A clinical photograph showing a skin lesion; a female subject in their 50s:
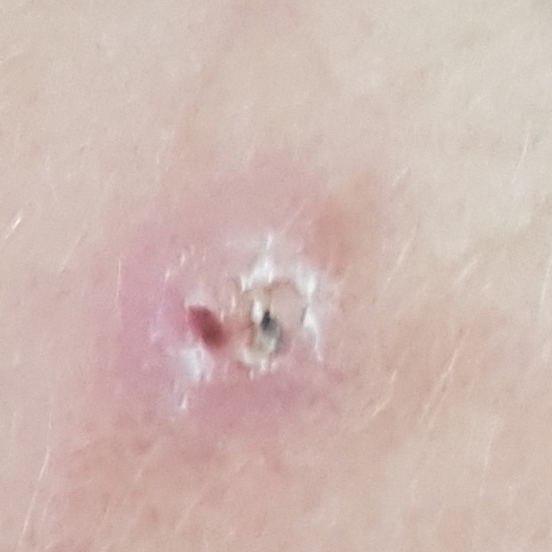Located on the face.
The patient reports that the lesion itches, but has not bled and has not grown.
The biopsy diagnosis was an actinic keratosis.